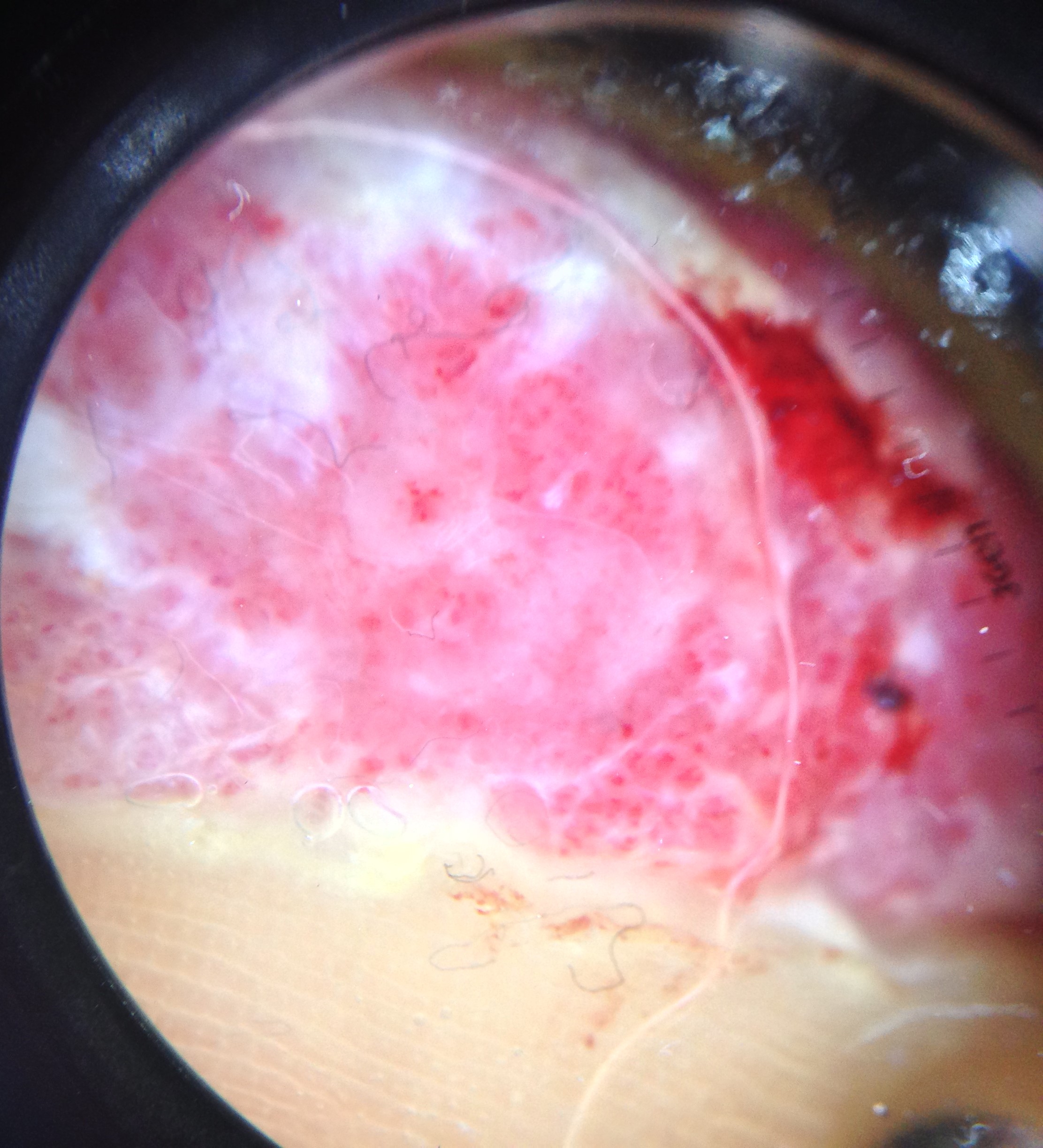image: dermoscopy; diagnostic label: acral nodular melanoma (biopsy-proven).